A dermoscopic close-up of a skin lesion.
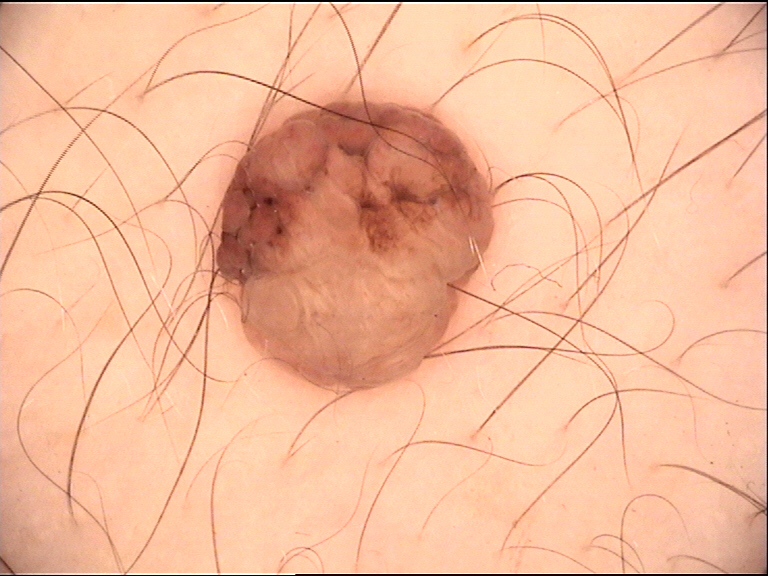classification: banal | diagnostic label: dermal nevus (expert consensus).